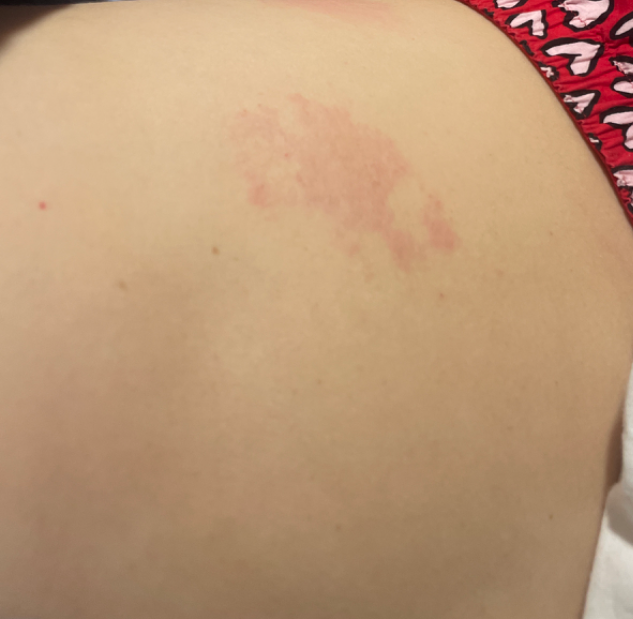Located on the back of the torso, leg and front of the torso.
The subject is a female aged 30–39.
This image was taken at a distance.
A single dermatologist reviewed the case: the favored diagnosis is Herpes Zoster; also consider Acute dermatitis, NOS.